Collected as part of a research study, without a referral diagnosis · the patient says their skin tans without first burning · the patient describes having a moderate number of moles · a dermatoscopic image of a skin lesion — 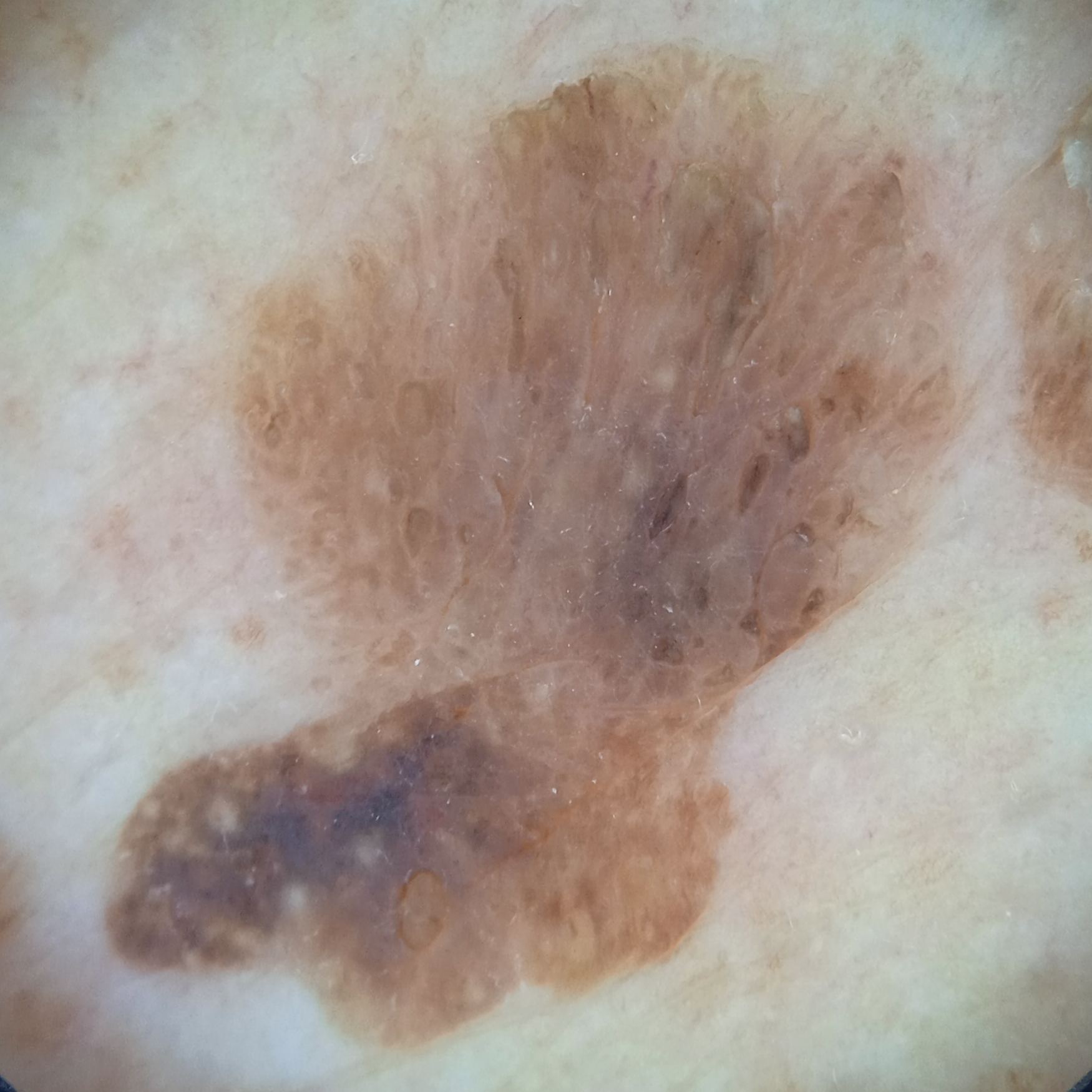Located on the back.
Measuring roughly 12.8 mm.
Dermatologist review favored a seborrheic keratosis.